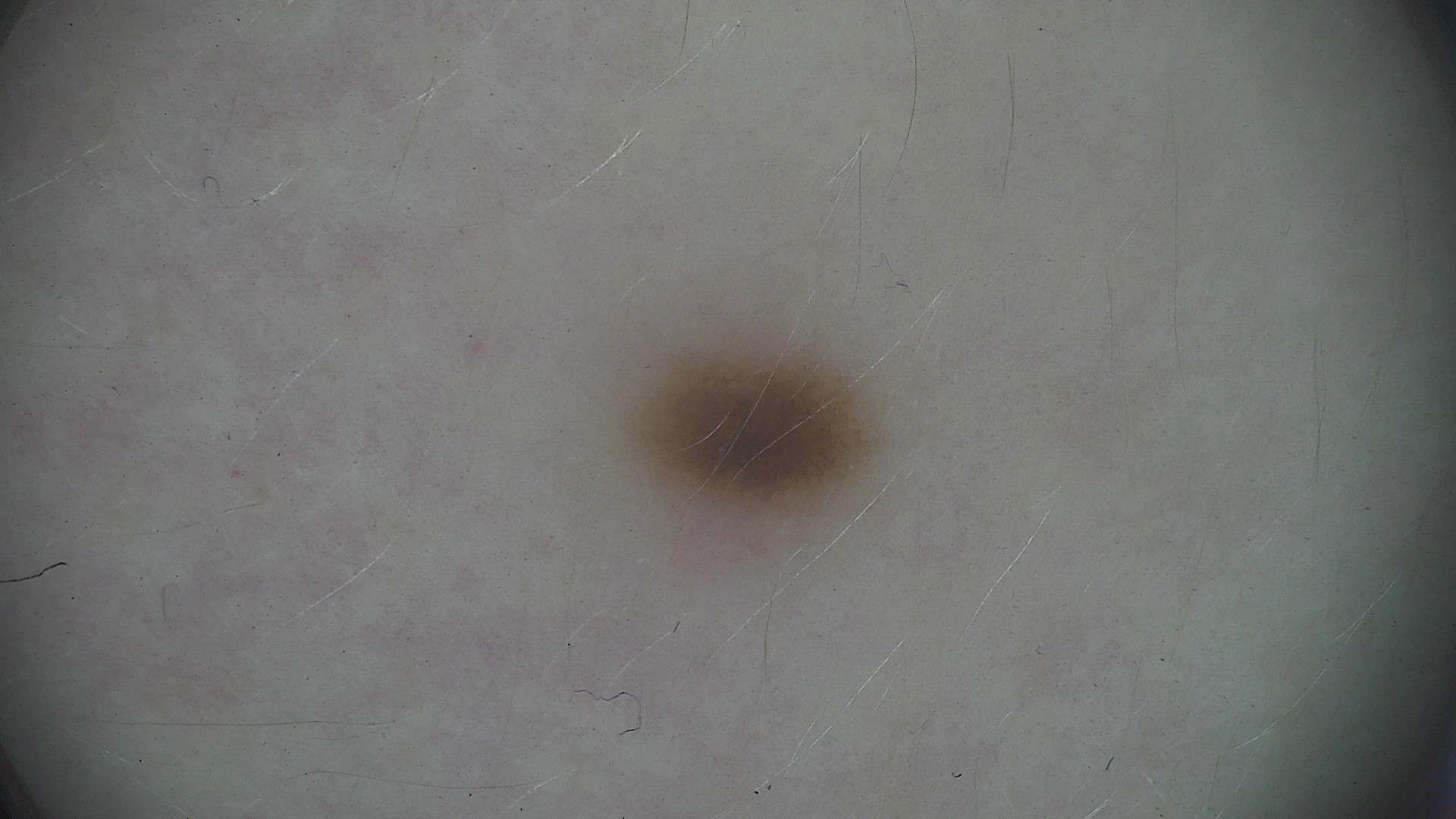Consistent with a dysplastic junctional nevus.